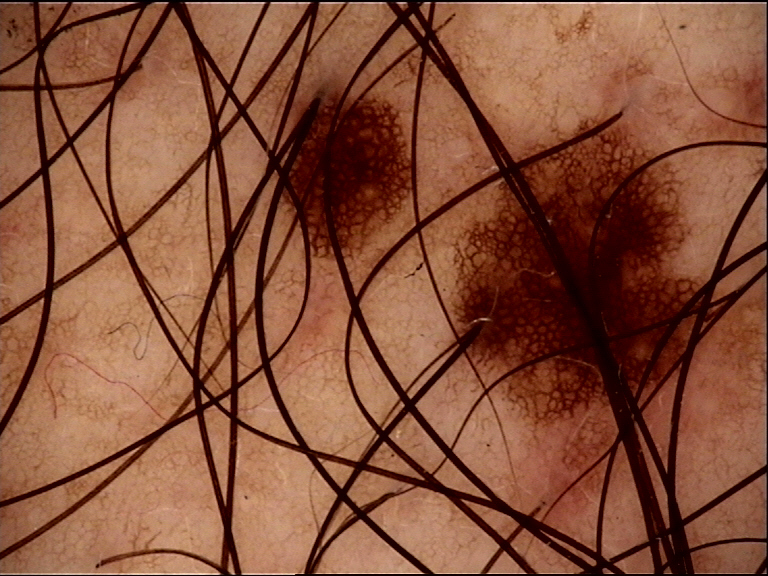Classified as a benign lesion — a dysplastic junctional nevus.